A close-up photograph.
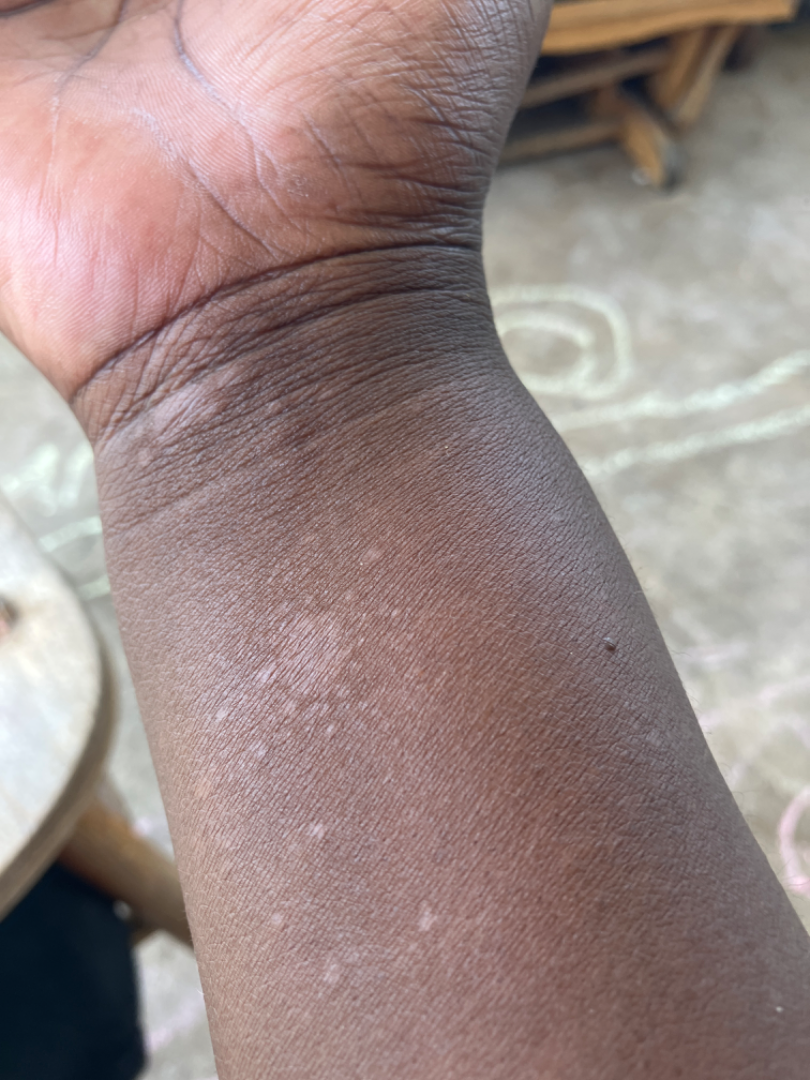One reviewing dermatologist: the impression was split between Chronic dermatitis, NOS and Allergic Contact Dermatitis.